The patient is 18–29, male · this is a close-up image.
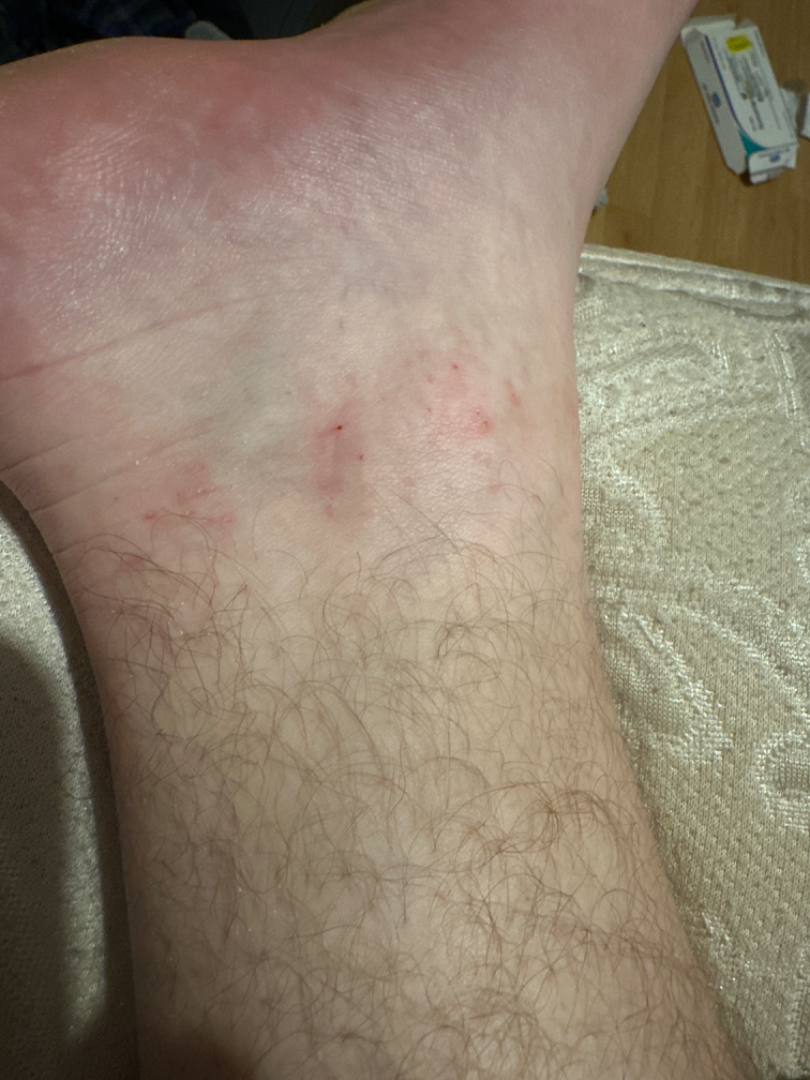<case>
<assessment>indeterminate</assessment>
</case>